The photograph was taken at an angle. The contributor is a female aged 40–49. The back of the hand, head or neck, leg and front of the torso are involved:
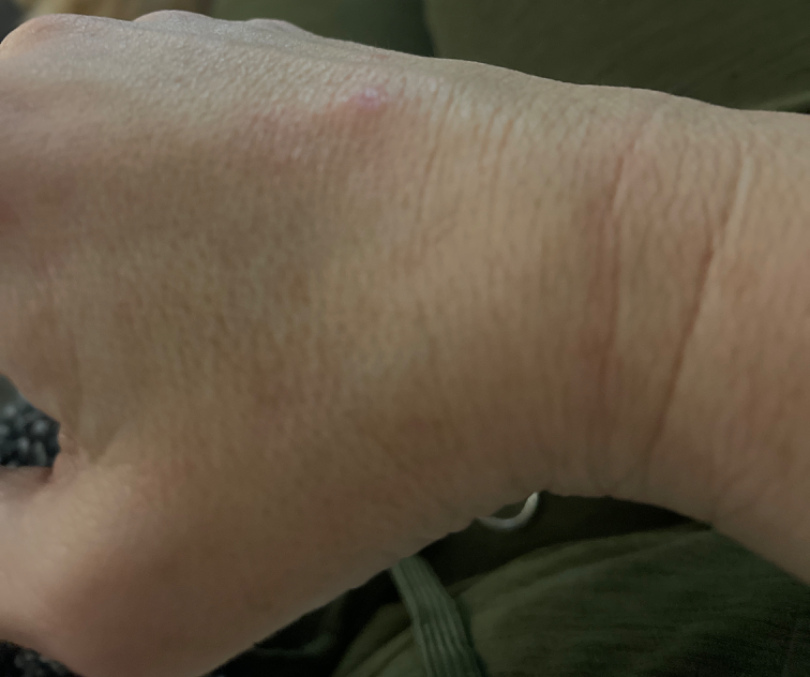Single-reviewer assessment: favoring Eczema; possibly Granuloma annulare.